A clinical close-up of a skin lesion · the patient says their skin tans without first burning · on a questionnaire the patient reported a personal history of skin cancer and a personal history of cancer · referred for assessment of suspected basal cell carcinoma · a female patient 60 years of age · few moles overall by the patient's own estimate:
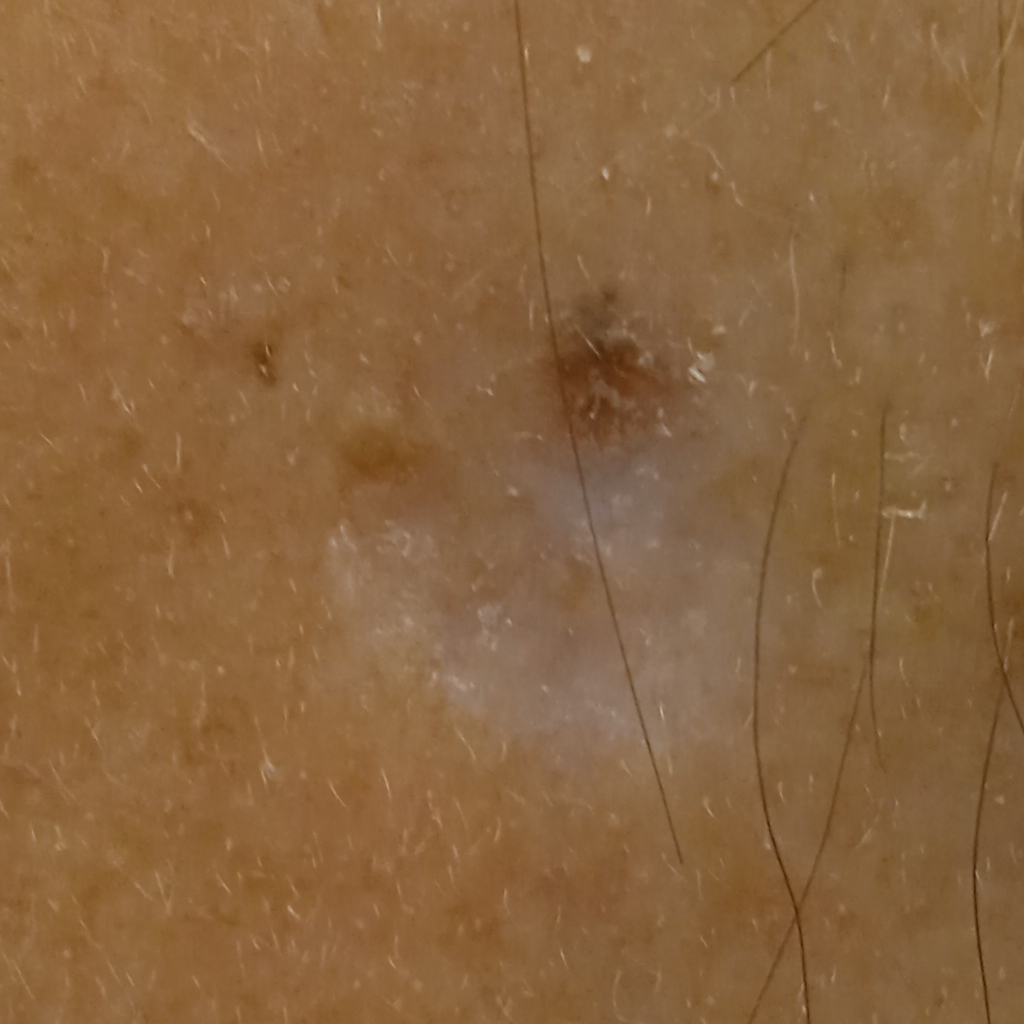Case summary: Located on the face. Diagnosis: Histopathology confirmed a basal cell carcinoma, following excision, with a measured tumor thickness of 1 mm.